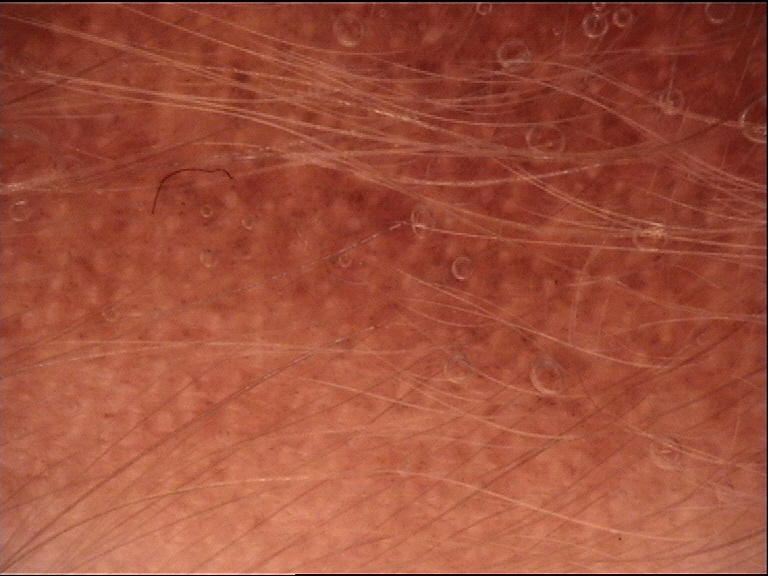modality — dermoscopy
subtype — banal
diagnosis — congenital junctional nevus (expert consensus)